A dermatoscopic image of a skin lesion: 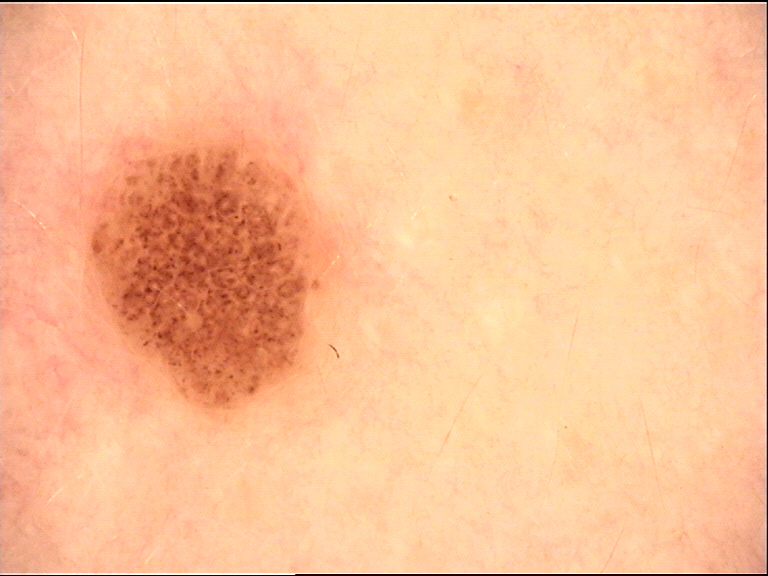Diagnosed as a dysplastic junctional nevus.